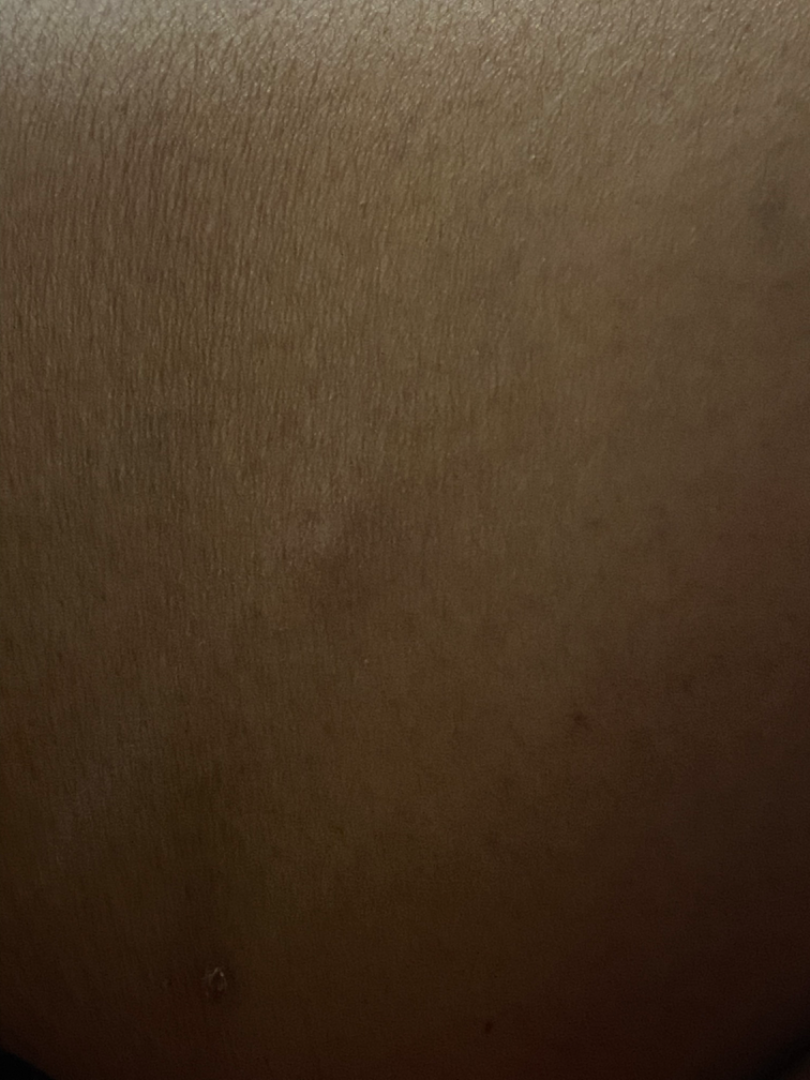Impression:
The skin findings could not be characterized from the image.